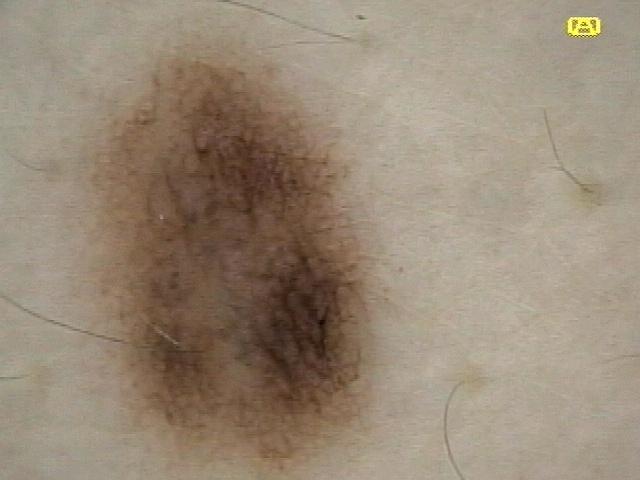A dermoscopic photograph of a skin lesion. A female patient aged approximately 40. Located on the anterior trunk. Histopathology confirmed a nevus.